A clinical photograph of a skin lesion · a subject in their 80s: 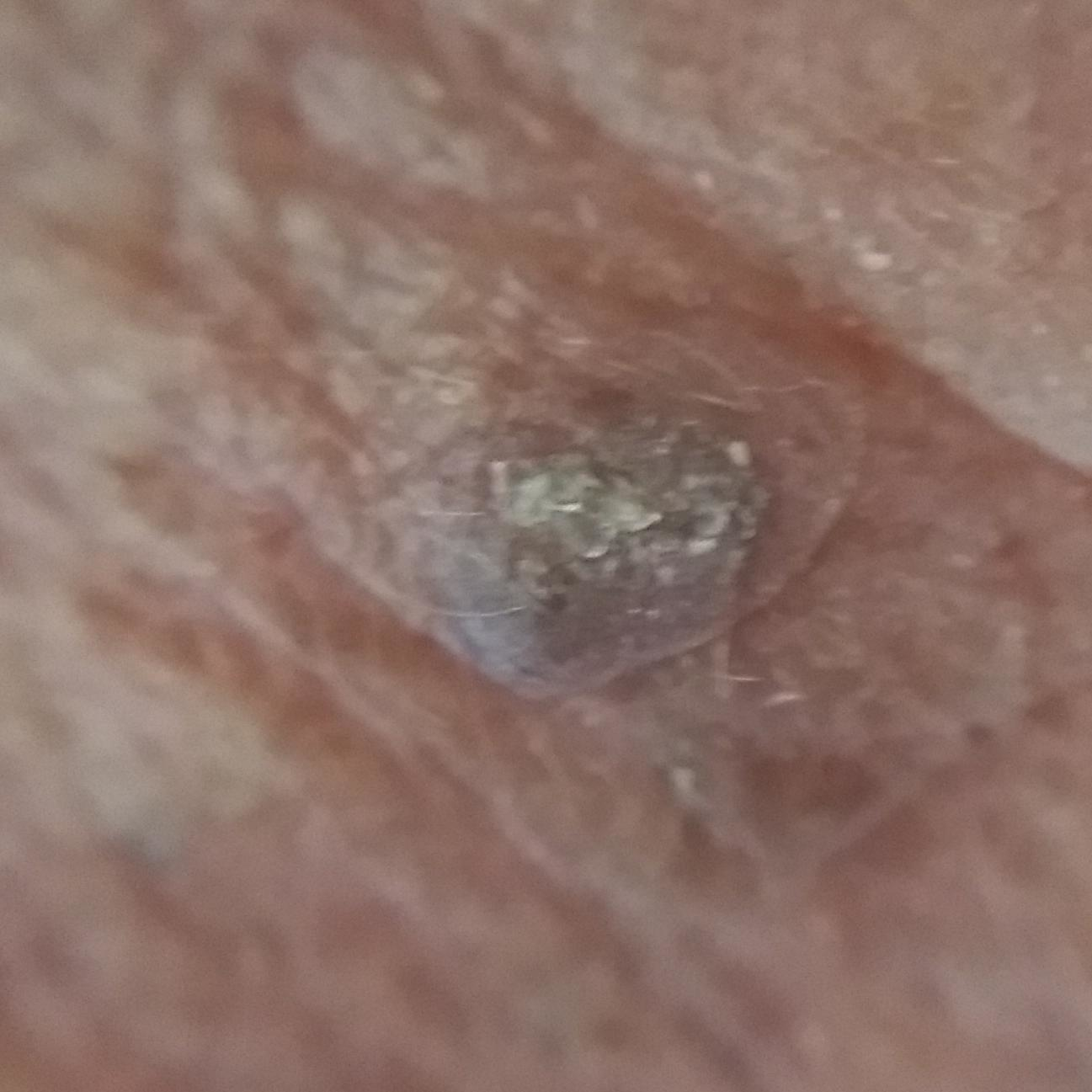location=the face
patient-reported symptoms=elevation
diagnostic label=seborrheic keratosis (clinical consensus)